Female patient, age 60–69. This image was taken at an angle. The arm is involved.
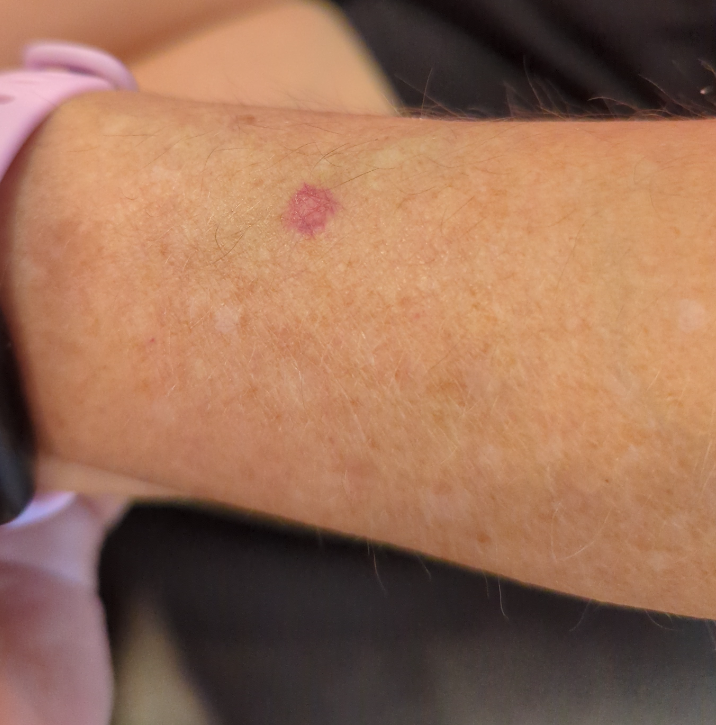Notes:
• assessment · indeterminate from the photograph